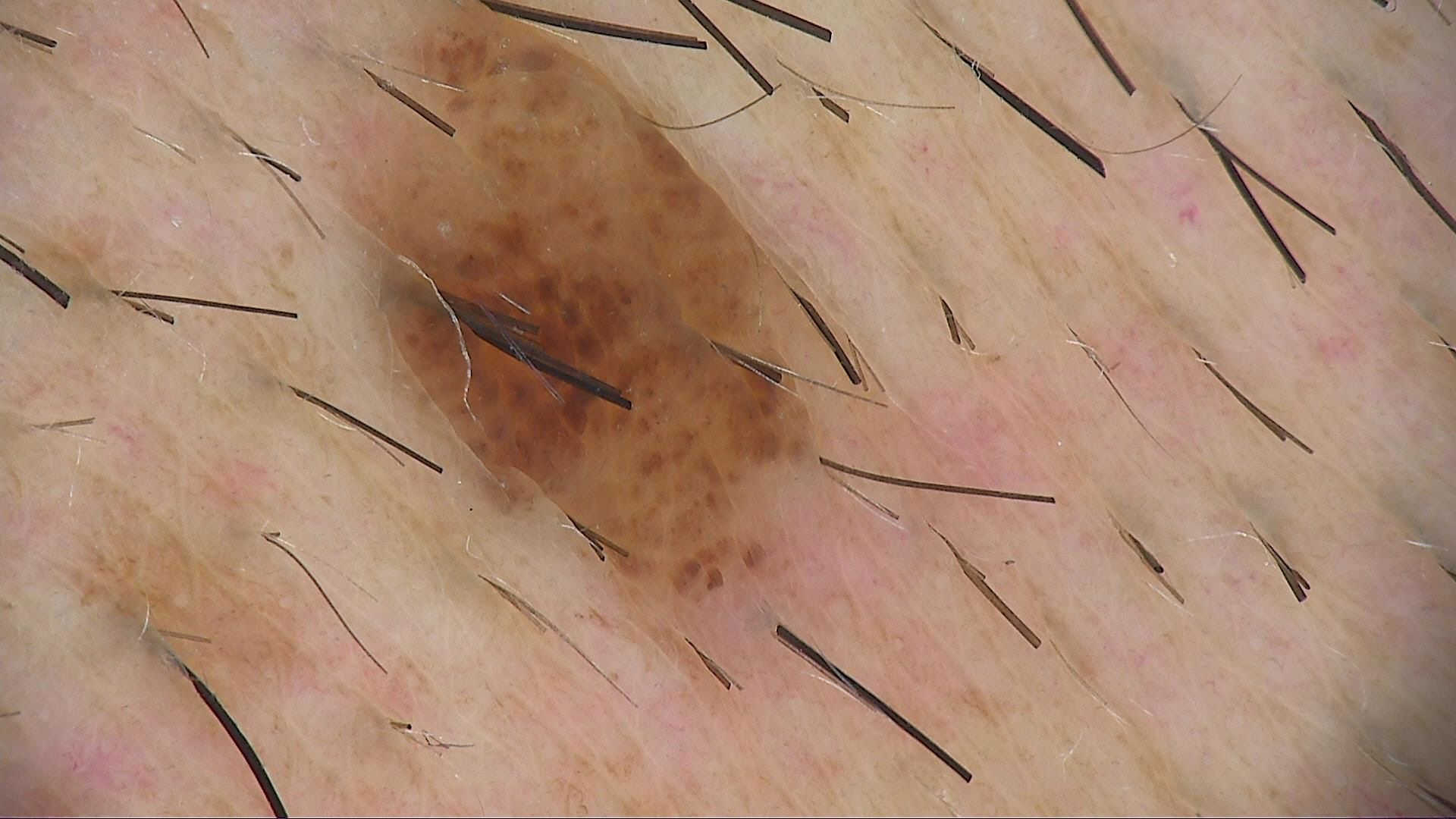<case>
  <lesion_type>
    <main_class>banal</main_class>
    <pattern>compound</pattern>
  </lesion_type>
  <diagnosis>
    <name>compound nevus</name>
    <code>cb</code>
    <malignancy>benign</malignancy>
    <super_class>melanocytic</super_class>
    <confirmation>expert consensus</confirmation>
  </diagnosis>
</case>